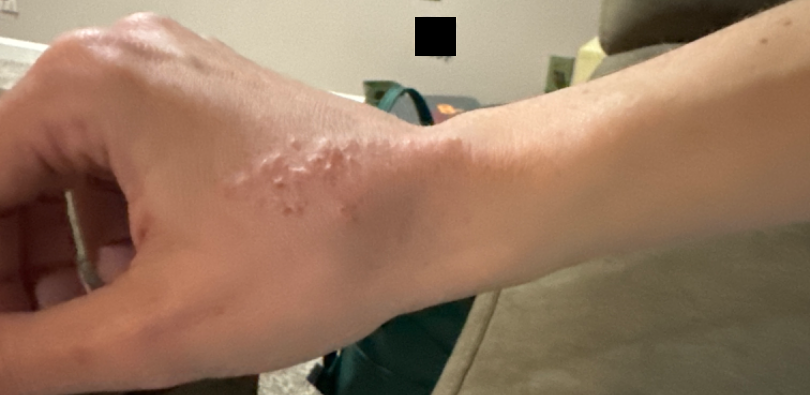view=at an angle | body site=back of the hand and arm | contributor=female, age 18–29 | differential diagnosis=Impetigo, Herpes Zoster and Herpes Simplex were each considered, in no particular order.